A dermatoscopic image of a skin lesion — 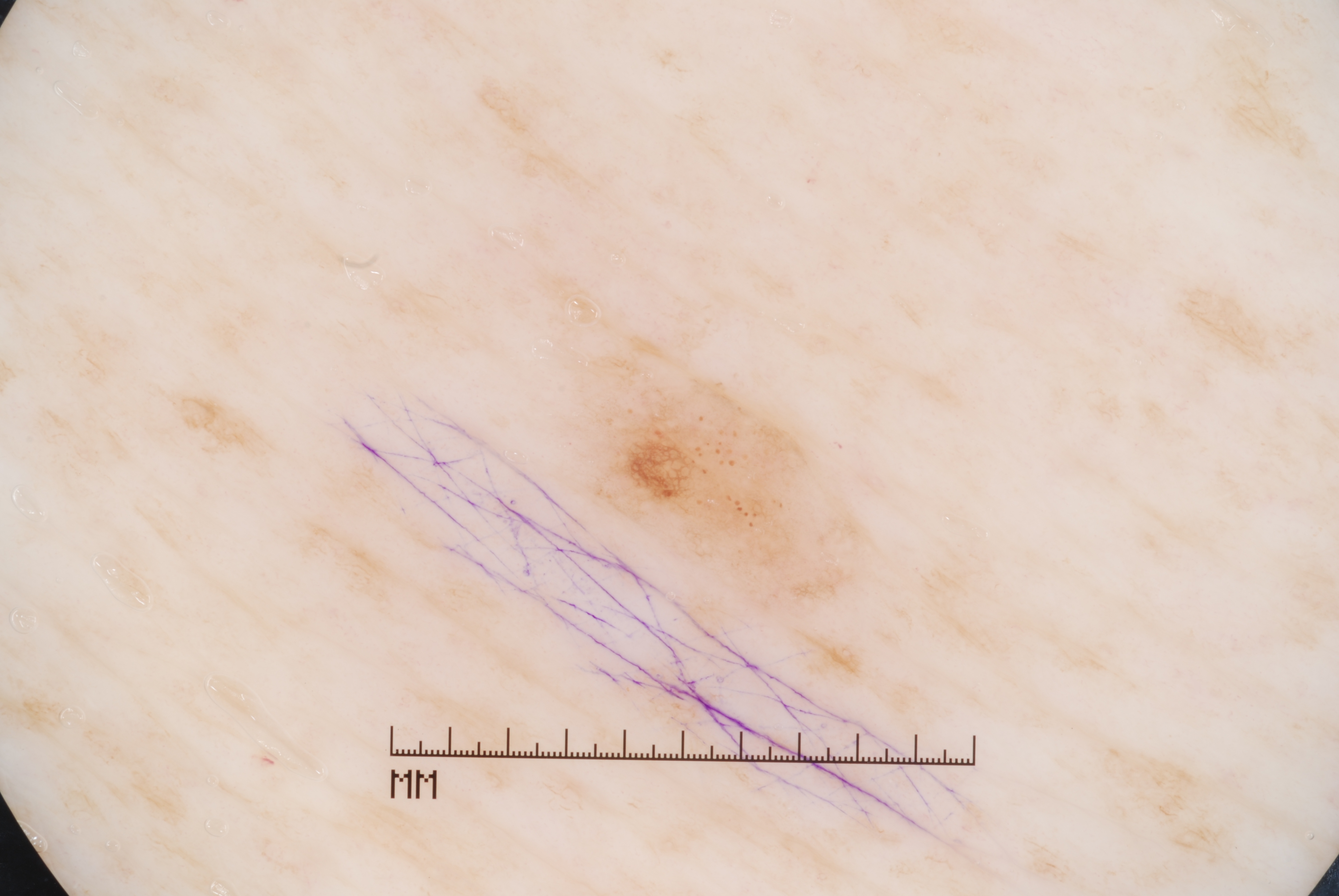On dermoscopy, the lesion shows pigment network, with no streaks, negative network, or milia-like cysts. With coordinates (x1, y1, x2, y2), the lesion occupies the region 586, 357, 837, 588. A small lesion occupying a minor part of the field. Consistent with a melanocytic nevus, a benign skin lesion.